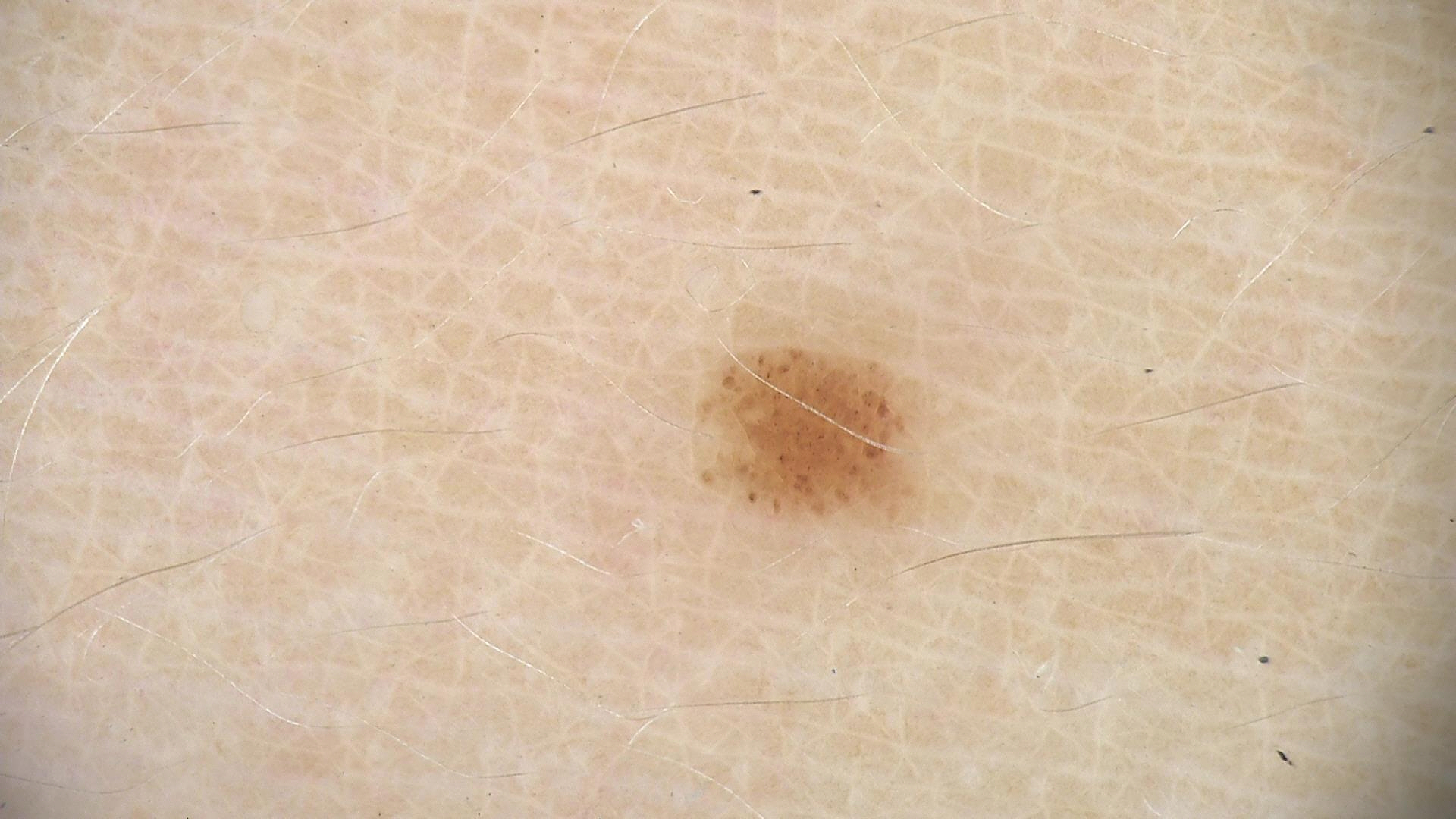Labeled as a dysplastic junctional nevus.